The photo was captured at a distance: 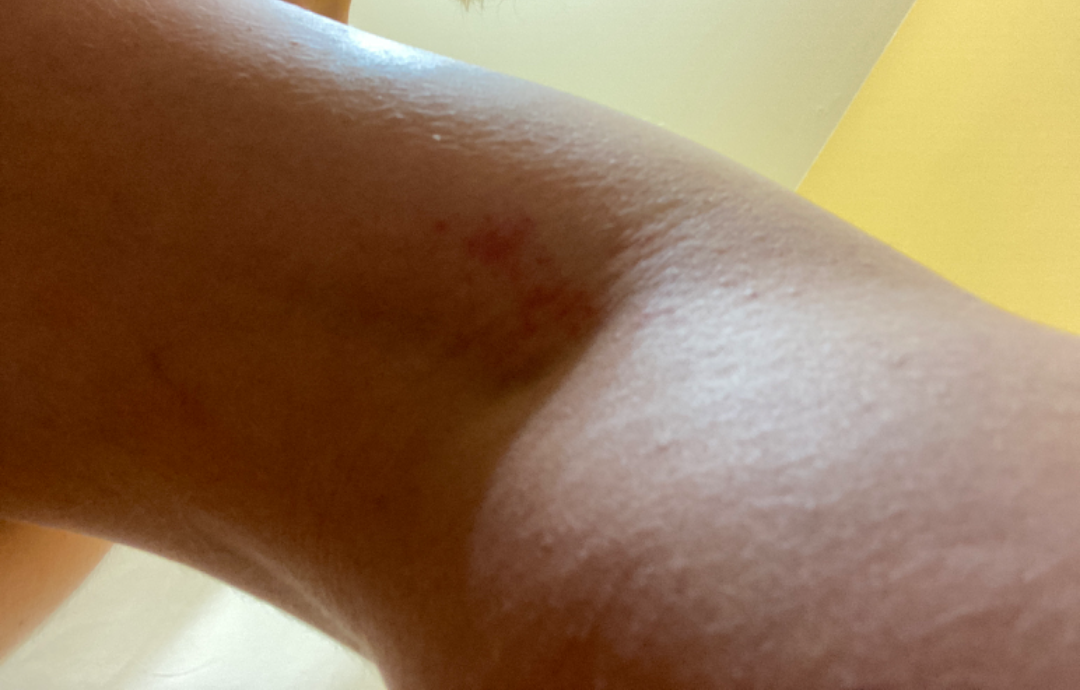Q: What is the dermatologist's impression?
A: Eczema (50%); Allergic Contact Dermatitis (50%)